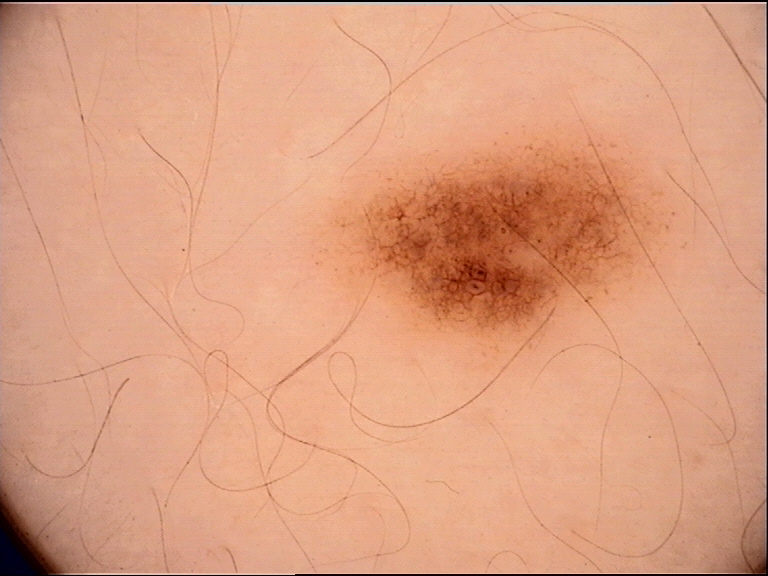Q: What is the imaging modality?
A: dermatoscopy
Q: What is the diagnosis?
A: dysplastic junctional nevus (expert consensus)